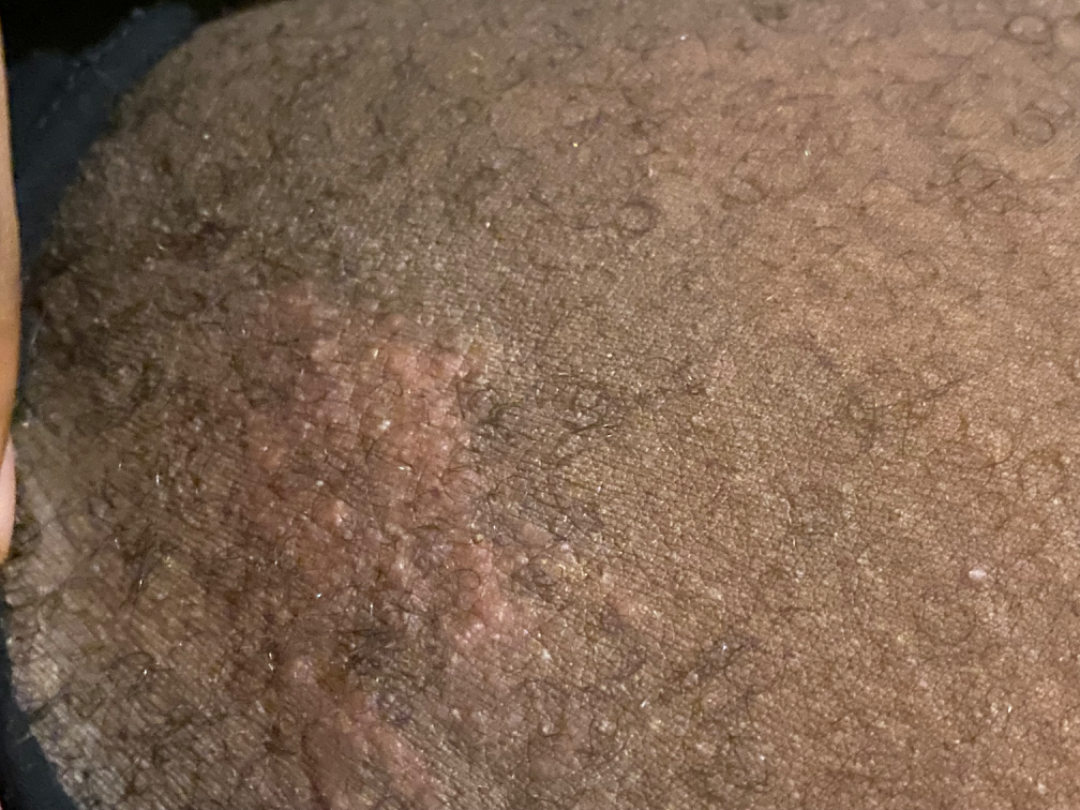Findings: The skin findings could not be characterized from the image. Background: The patient reports the lesion is rough or flaky. The photograph is a close-up of the affected area. Fitzpatrick VI; lay reviewers estimated MST 8 (US pool) or 5 (India pool).